A skin lesion imaged with a dermatoscope.
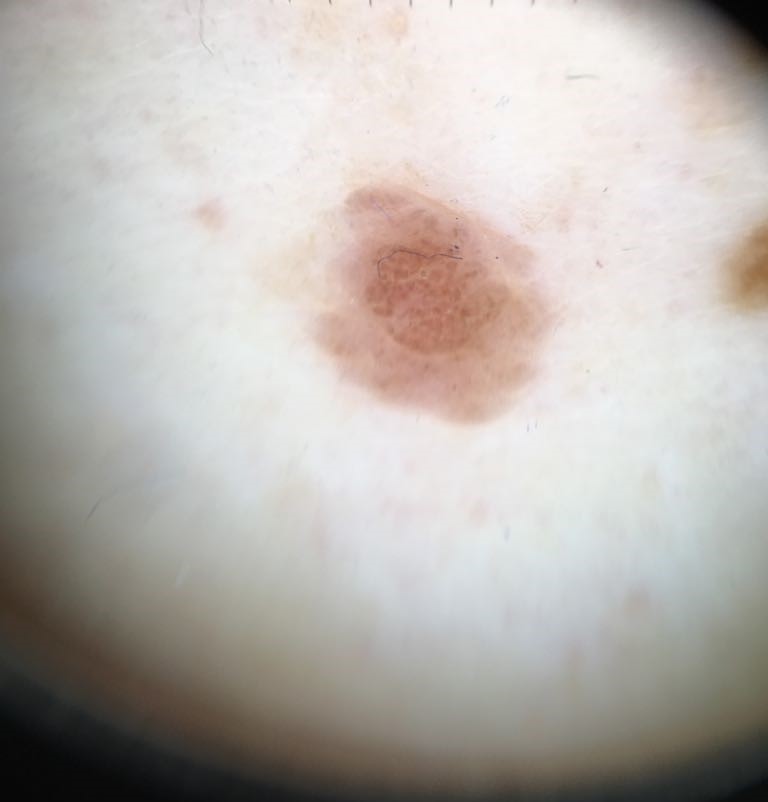category: banal; diagnostic label: compound nevus (expert consensus).